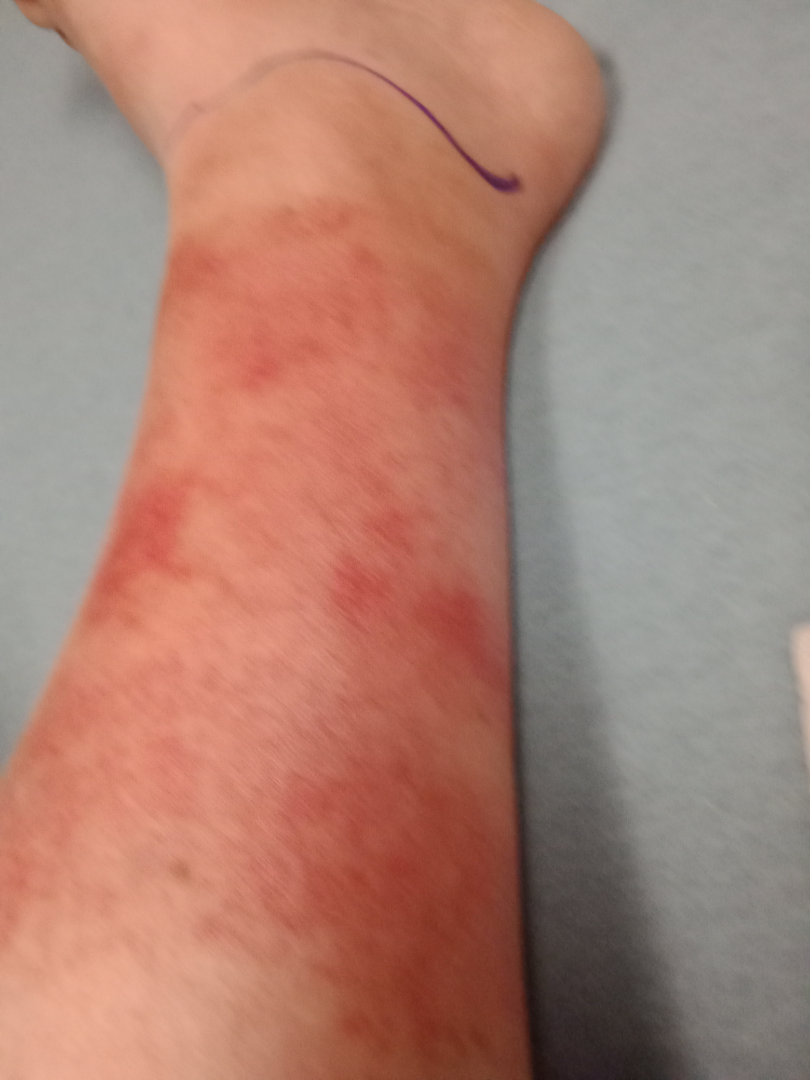Notes:
• subject · female, age 40–49
• location · top or side of the foot and leg
• framing · at an angle
• differential diagnosis · Cellulitis (0.39); Stasis Dermatitis (0.33); Pigmented purpuric eruption (0.28)